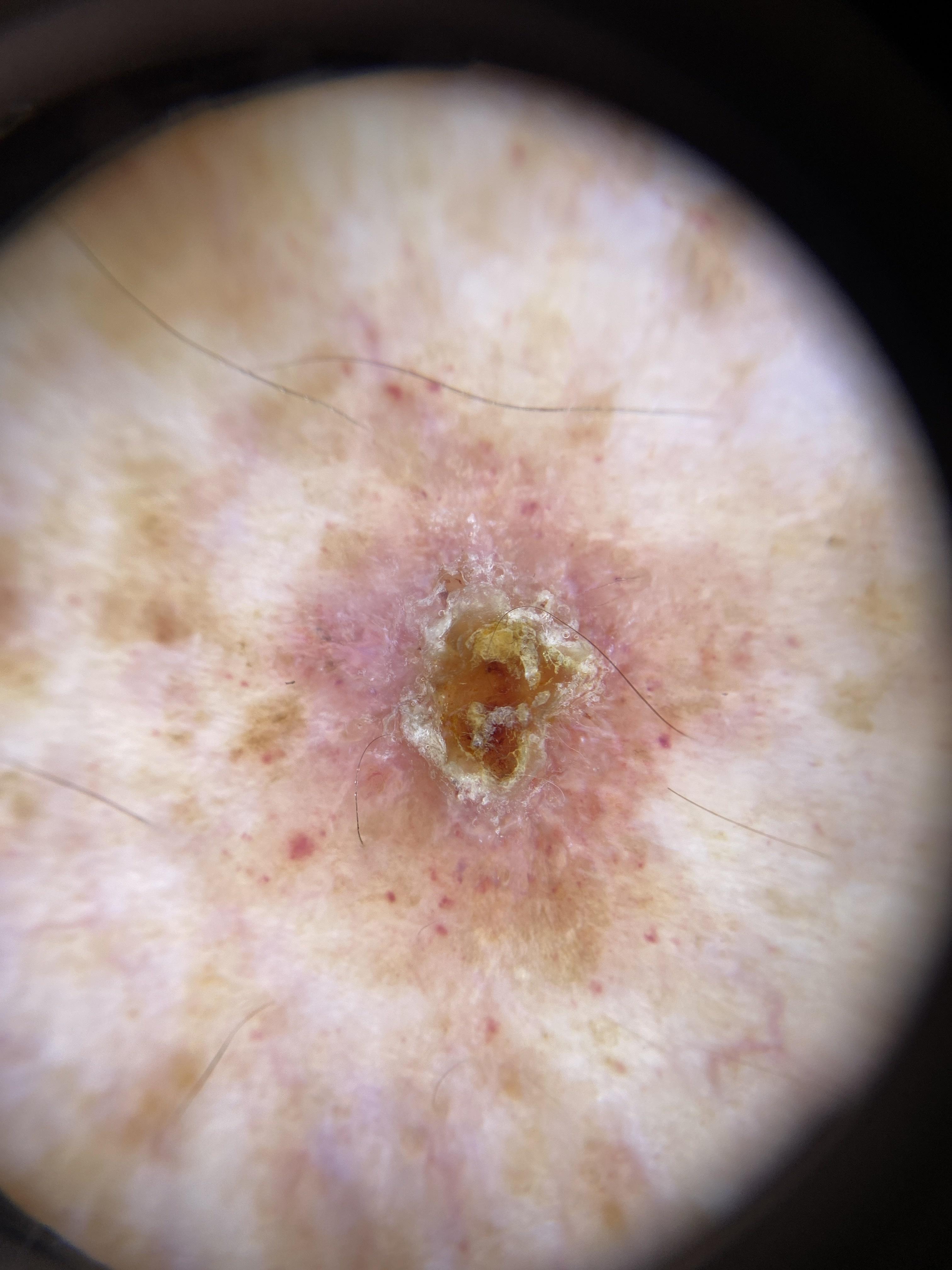{"image": "dermoscopy", "patient": {"age_approx": 70, "sex": "male"}, "skin_type": "II", "lesion_location": {"region": "a lower extremity"}, "diagnosis": {"name": "Basal cell carcinoma", "malignancy": "malignant", "confirmation": "histopathology", "lineage": "adnexal"}}